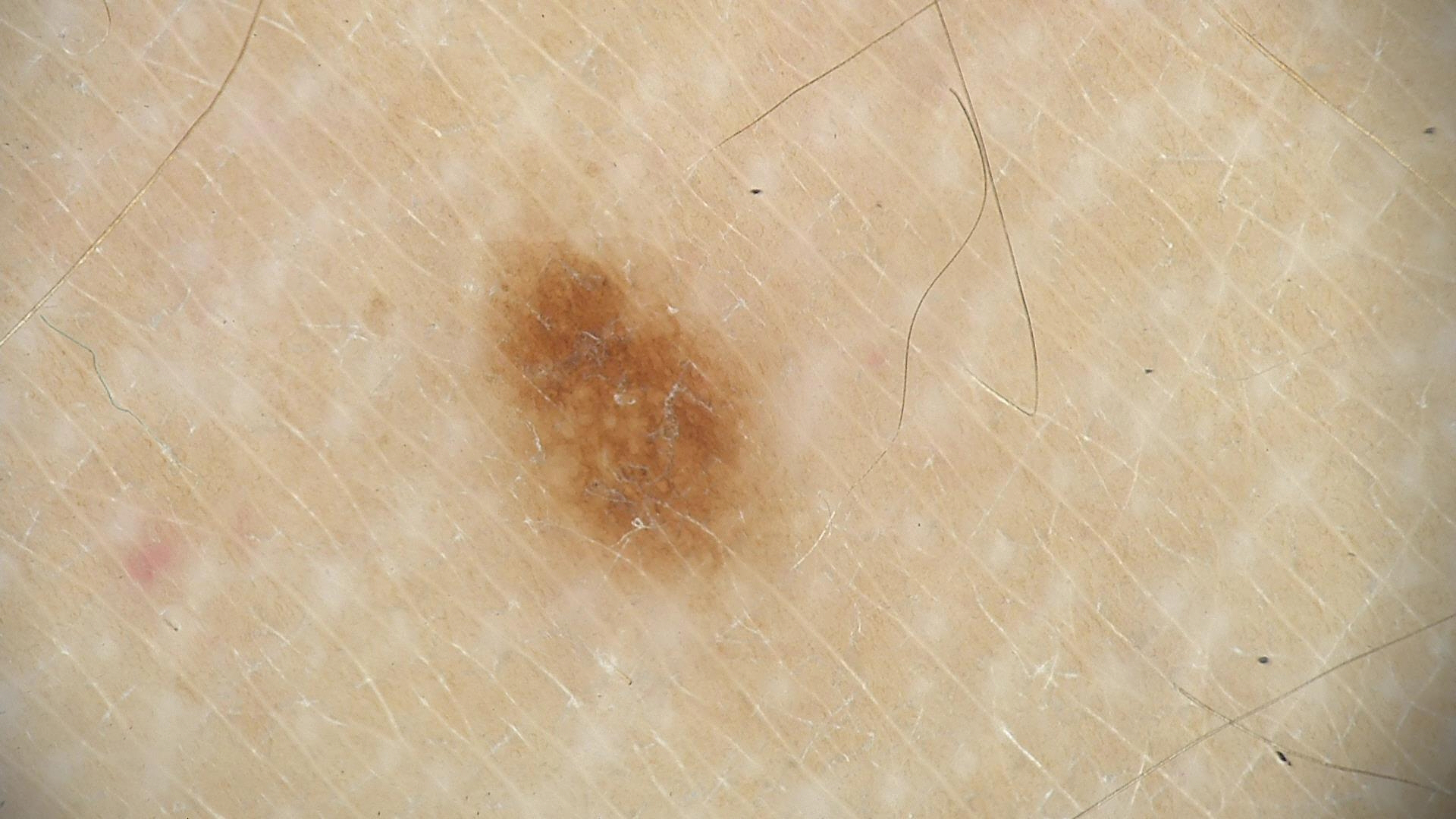{"diagnosis": {"name": "dysplastic junctional nevus", "code": "jd", "malignancy": "benign", "super_class": "melanocytic", "confirmation": "expert consensus"}}